Few moles overall by the patient's own estimate; a female subject 68 years old; collected as part of a research study, without a referral diagnosis; on a questionnaire the patient reported no immunosuppression; the patient says their skin tans without first burning:
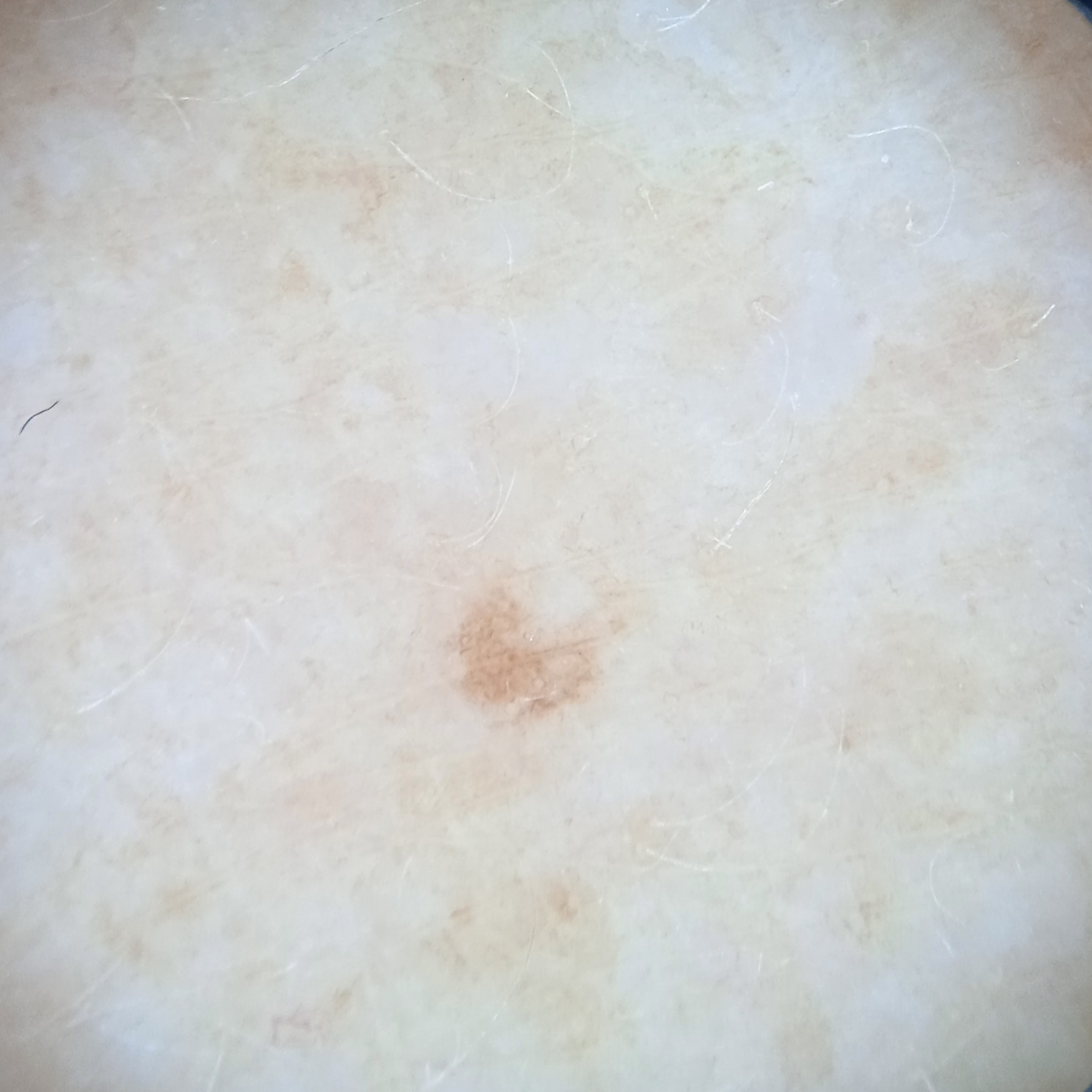size = 1.7 mm, assessment = melanocytic nevus (dermatologist consensus).